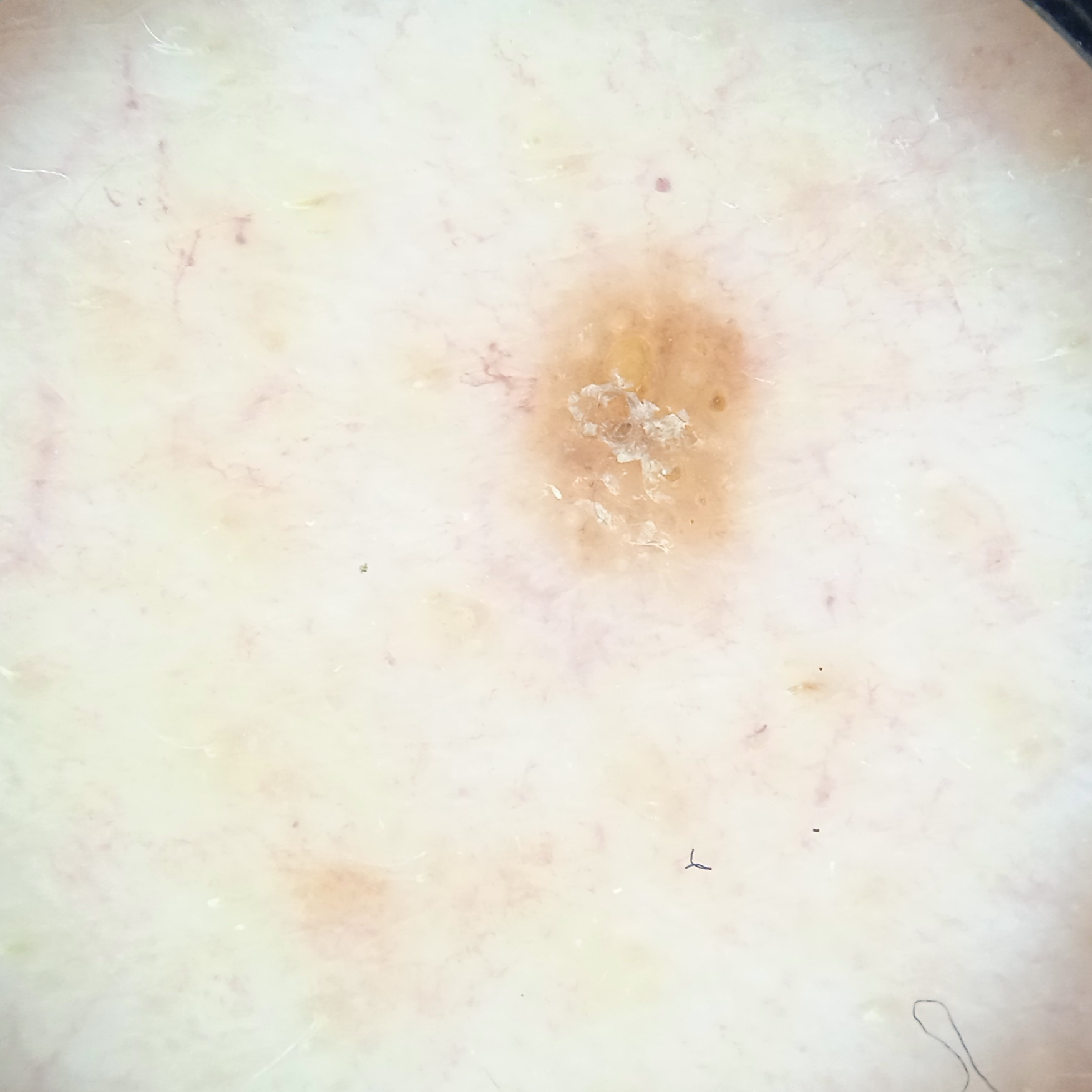Q: Why was this imaged?
A: research study (no referral diagnosis)
Q: Patient demographics?
A: male, age 65
Q: What is the imaging modality?
A: dermatoscopic image
Q: What is the anatomic site?
A: the back
Q: What was the diagnosis?
A: melanocytic nevus (dermatologist consensus)